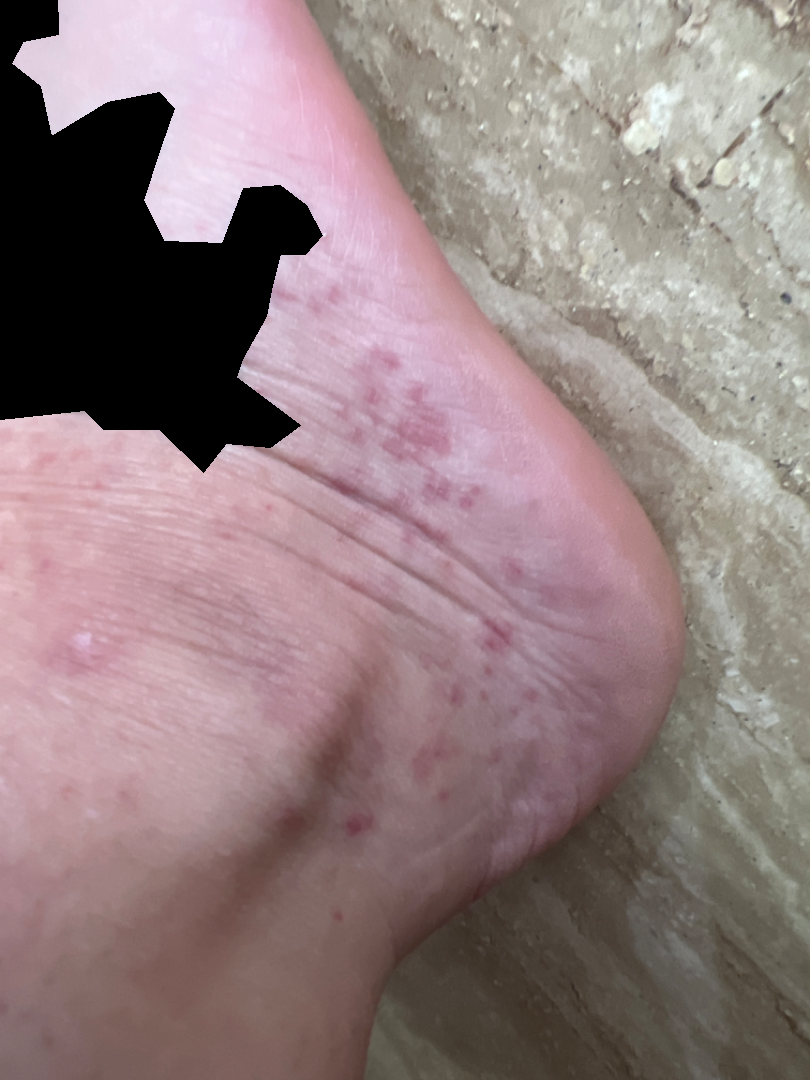| key | value |
|---|---|
| reported symptoms | bothersome appearance |
| skin tone | FST II |
| onset | less than one week |
| image framing | close-up |
| contributor | female, age 30–39 |
| body site | leg, back of the hand, top or side of the foot and sole of the foot |
| systemic symptoms | joint pain |
| differential diagnosis | most likely Lichen planus/lichenoid eruption; possibly Psoriasis; with consideration of Eczema |